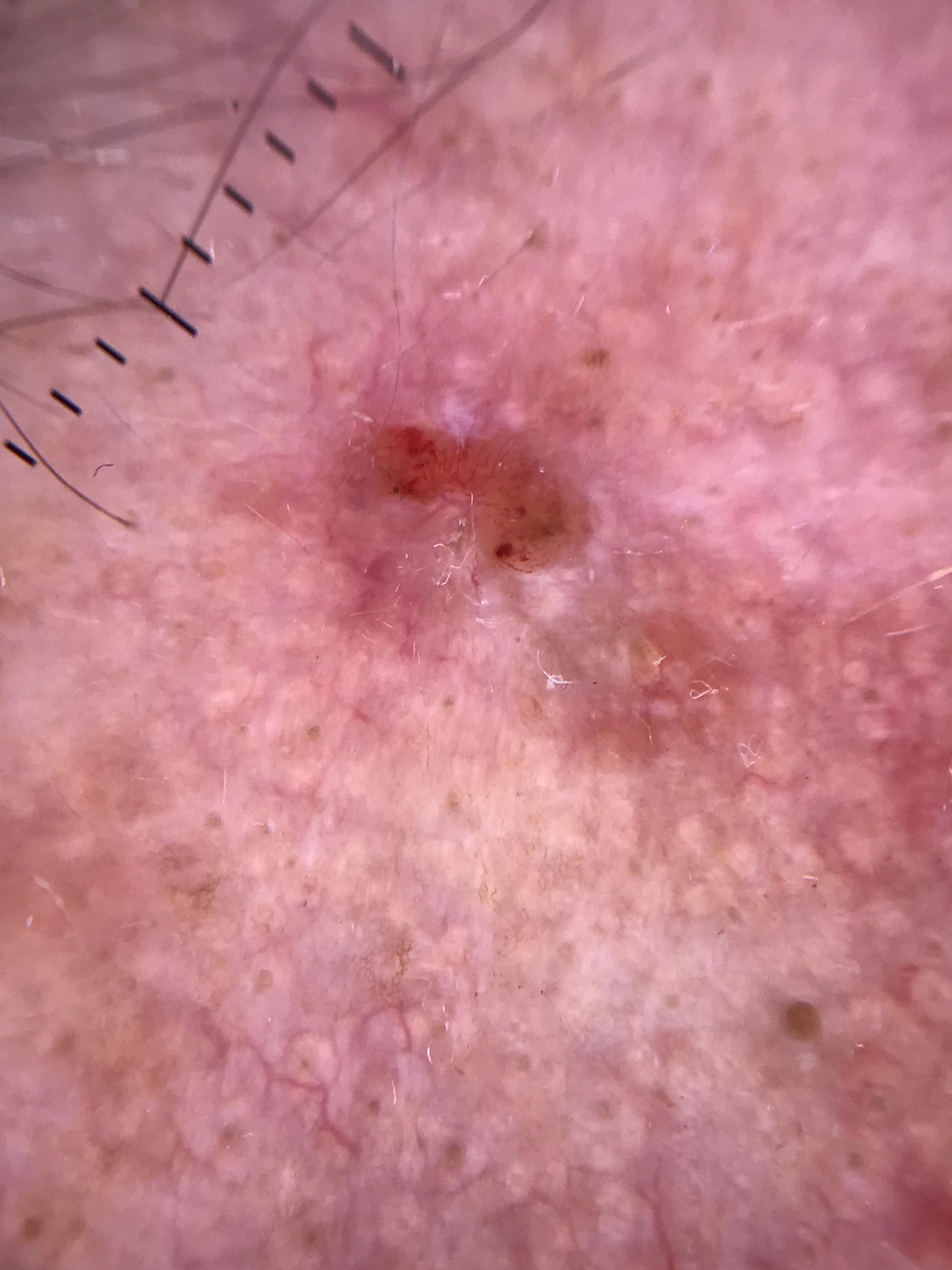Q: Who is the patient?
A: male, about 70 years old
Q: What is the patient's skin type?
A: II
Q: What is the imaging modality?
A: contact-polarized dermoscopy
Q: What is this lesion?
A: Basal cell carcinoma (biopsy-proven)